A male patient, about 50 years old · dermoscopy of a skin lesion — 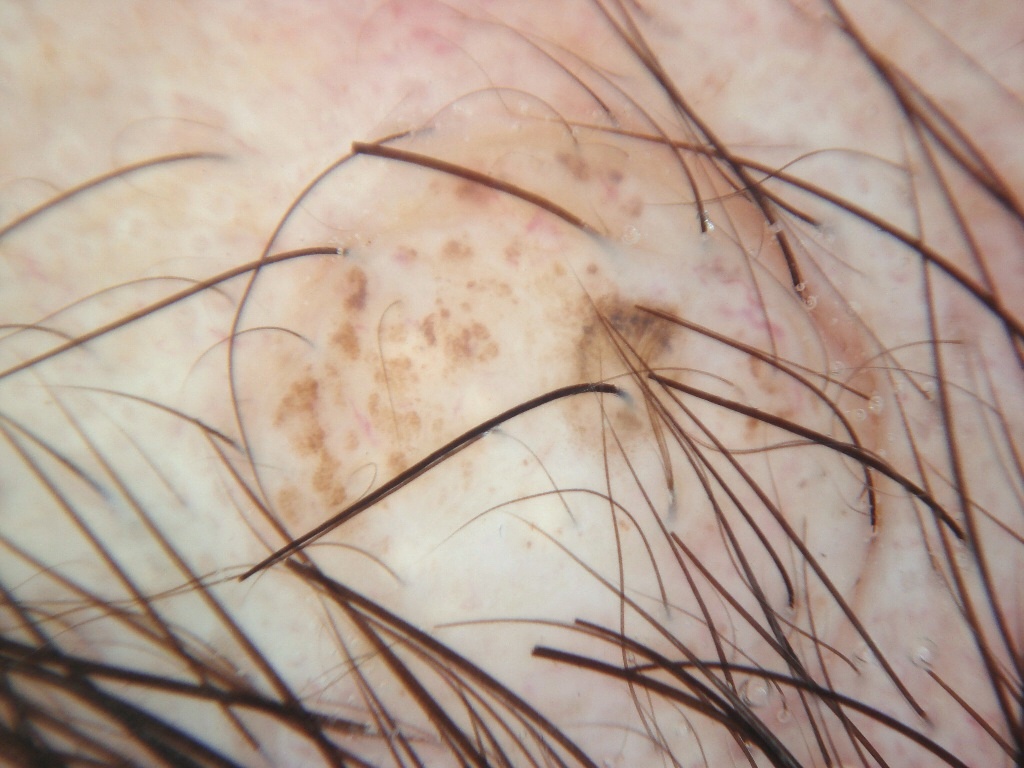Notes:
- dermoscopic pattern — globules; absent: negative network, streaks, milia-like cysts, and pigment network
- lesion location — box(227, 117, 884, 764)
- diagnostic label — a melanocytic nevus, a benign skin lesion